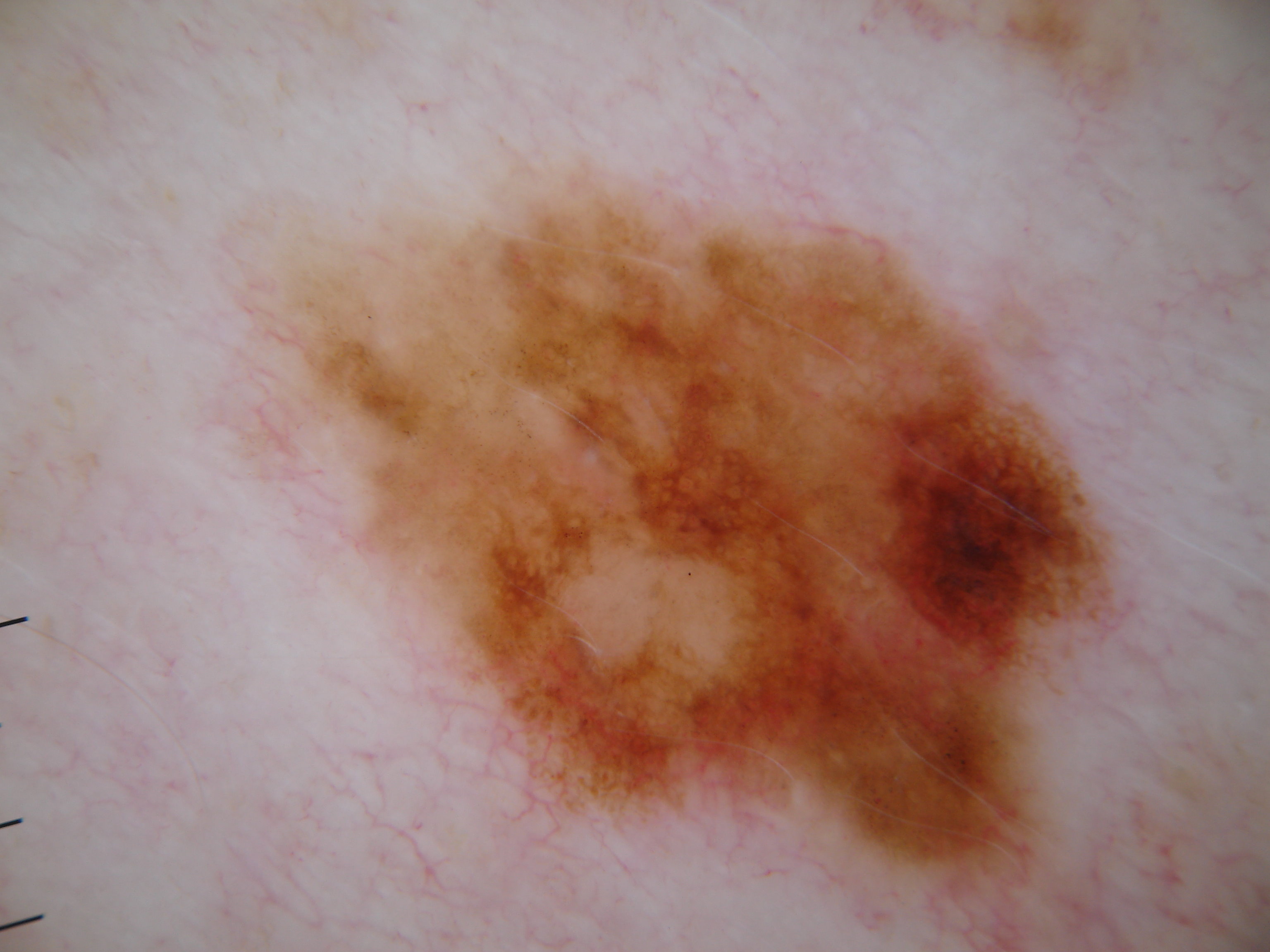{"image": {"modality": "dermoscopy"}, "lesion_location": {"bbox_xyxy": [214, 138, 1126, 918]}, "dermoscopic_features": {"present": ["pigment network", "globules"], "absent": ["streaks", "negative network", "milia-like cysts"]}, "lesion_extent": {"approx_field_fraction_pct": 39}, "diagnosis": {"name": "melanocytic nevus", "malignancy": "benign", "lineage": "melanocytic", "provenance": "clinical"}}